Close-up view. The affected area is the leg, head or neck, front of the torso, back of the torso and arm:
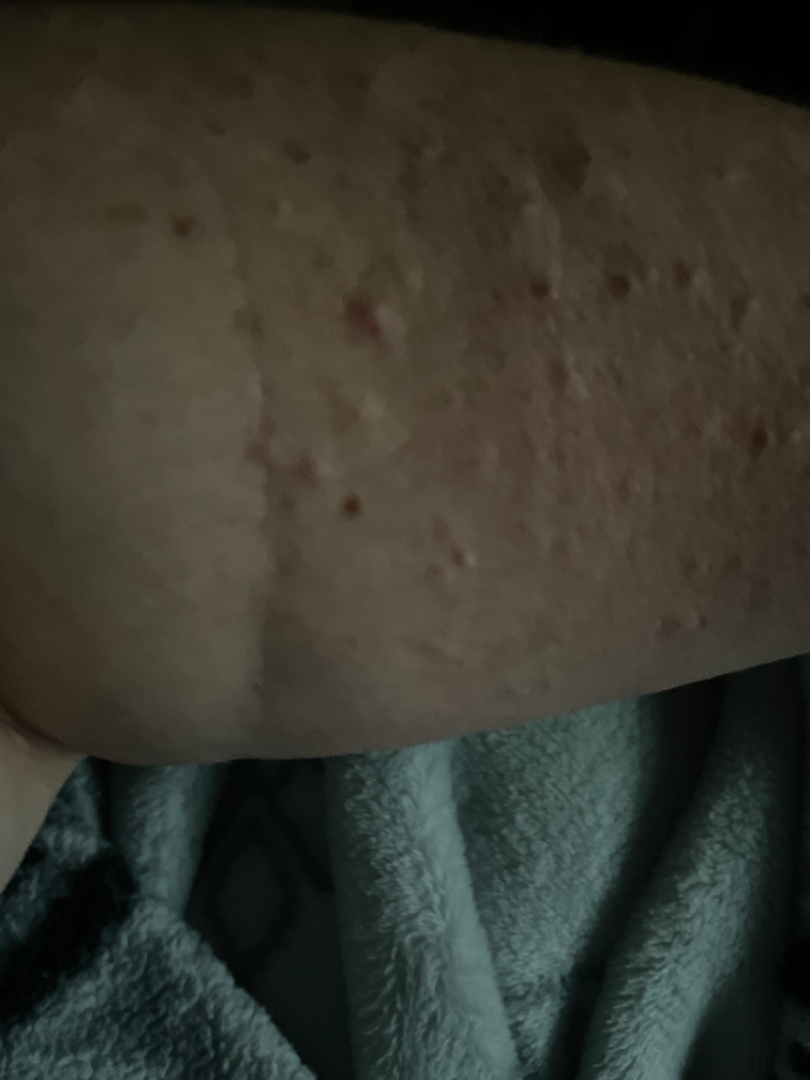assessment = indeterminate | self-categorized as = a rash | lesion symptoms = burning, bothersome appearance and itching | onset = less than one week | texture = raised or bumpy.